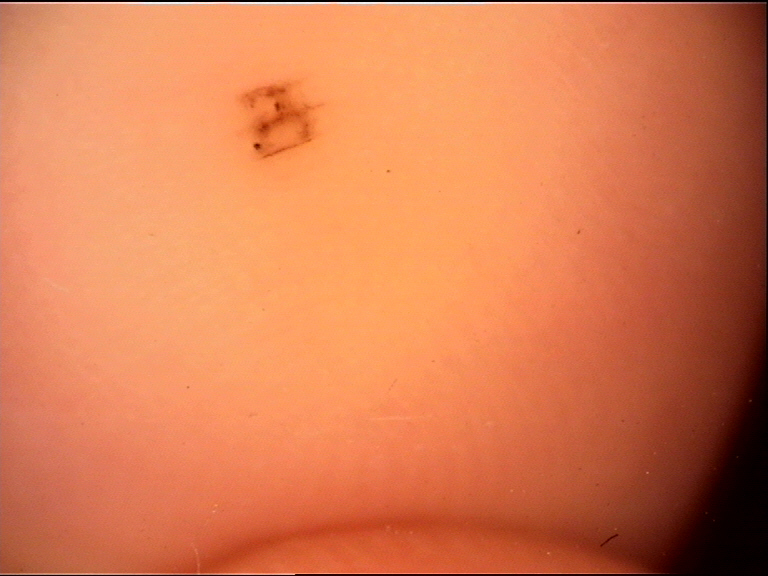diagnostic label = acral junctional nevus (expert consensus).